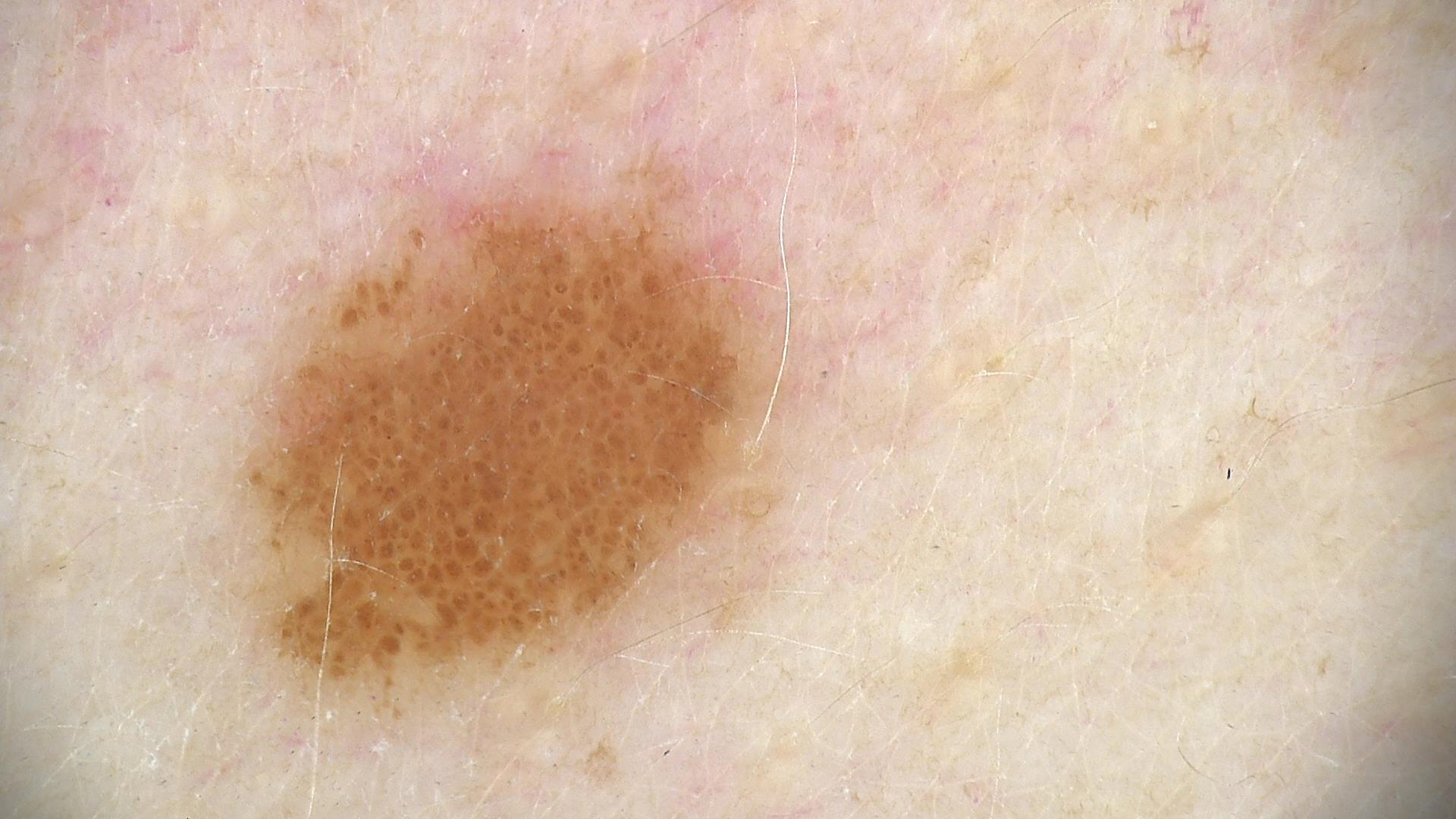modality = dermoscopy | classification = banal | class = junctional nevus (expert consensus).